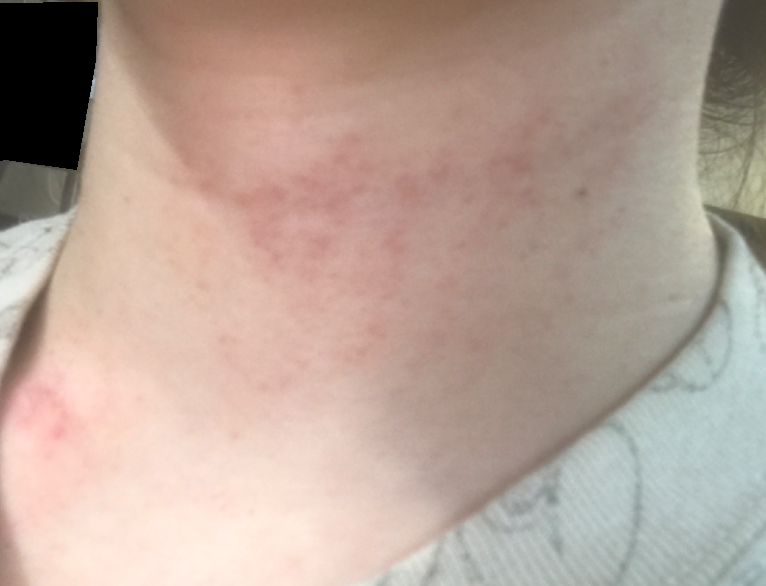The lesion is associated with bothersome appearance and itching.
Texture is reported as flat.
The subject is 18–29, female.
This is a close-up image.
Located on the head or neck.
The condition has been present for about one day.
On remote review of the image, Allergic Contact Dermatitis (weight 0.50); Irritant Contact Dermatitis (weight 0.50).